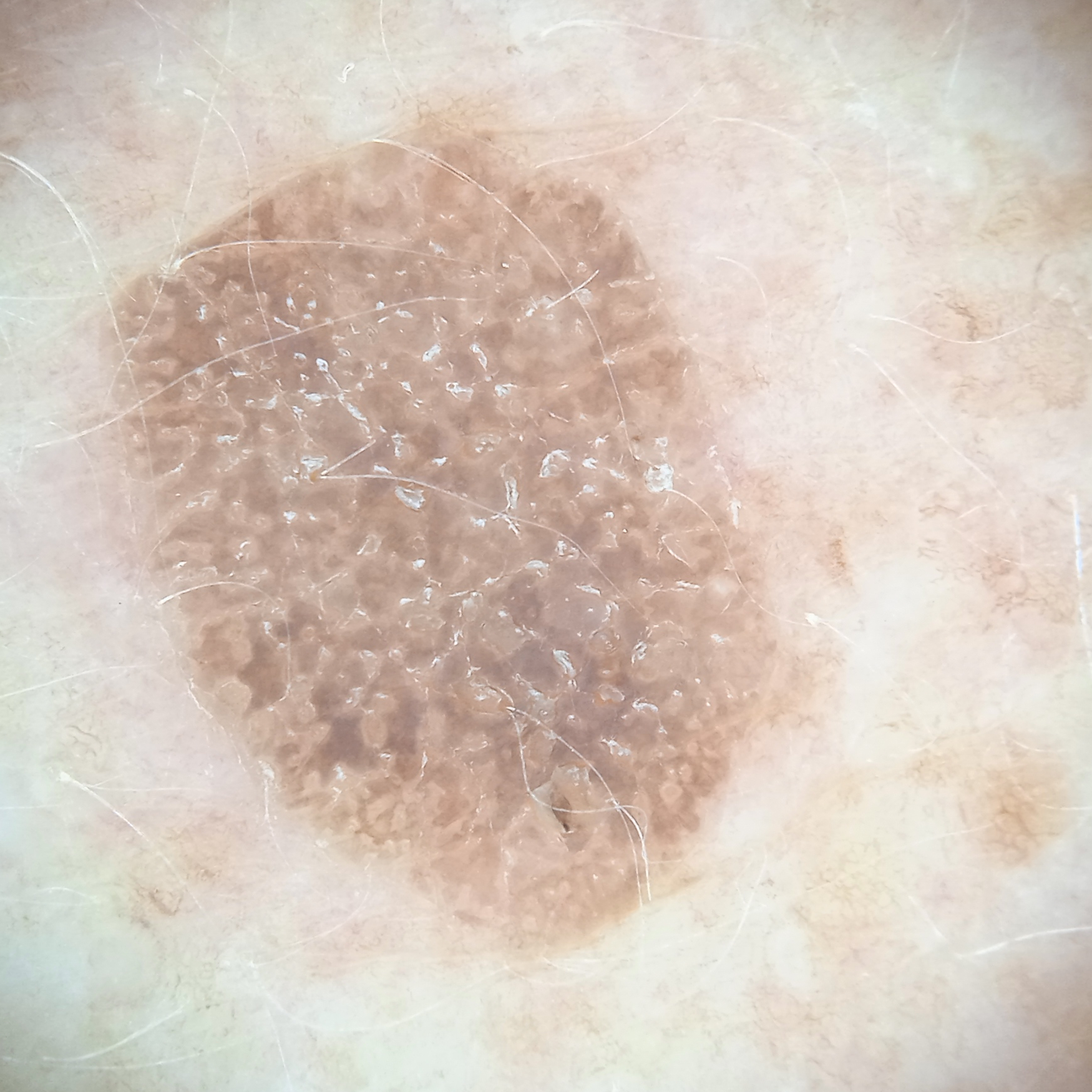assessment = seborrheic keratosis (dermatologist consensus)